A female patient age 78 · the chart notes prior malignancy (patient or family), no pesticide exposure, and no tobacco use · recorded as skin type III · a smartphone photograph of a skin lesion: 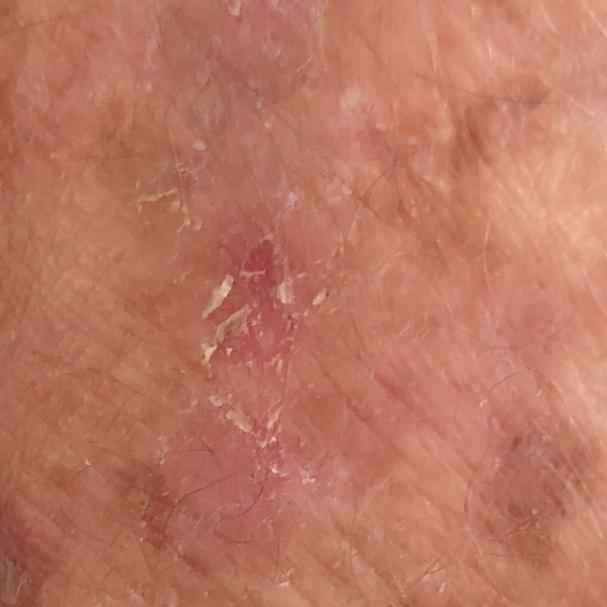Notes:
• region — a forearm
• diameter — 11 × 6 mm
• symptoms — itching / no elevation
• diagnosis — actinic keratosis (clinical consensus)